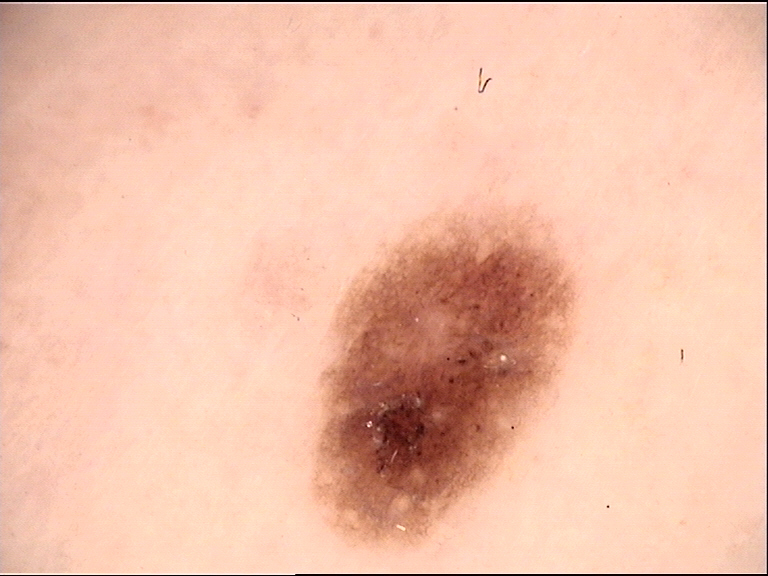Findings:
A dermatoscopic image of a skin lesion.
Impression:
The diagnostic label was a dysplastic junctional nevus.